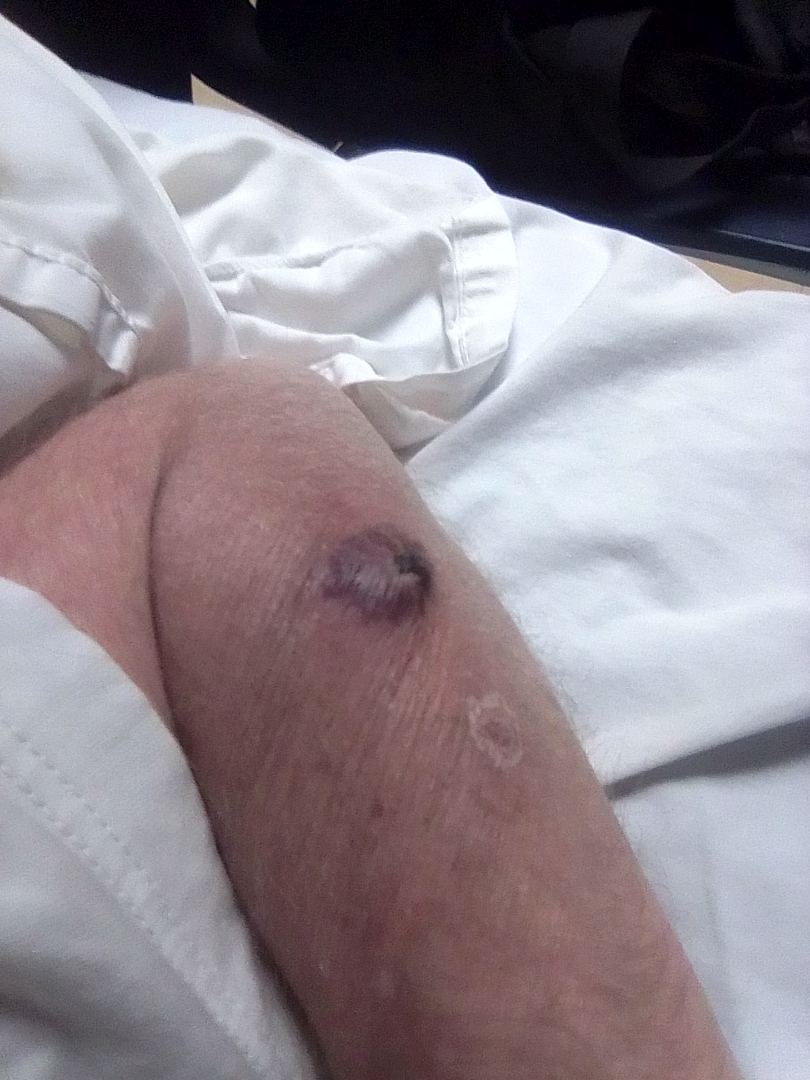Case summary:
- assessment: ungradable on photographic review